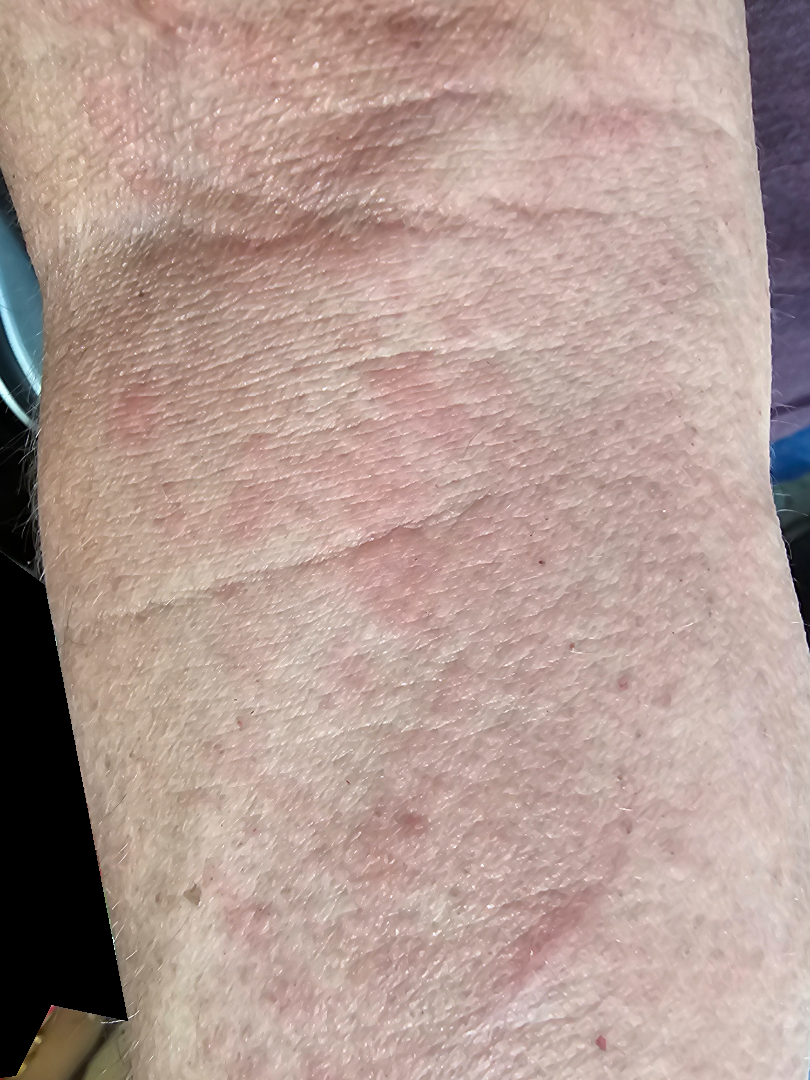Clinical context:
Reported lesion symptoms include itching and enlargement. Located on the front of the torso and arm. The photograph is a close-up of the affected area. Fitzpatrick skin type III; lay reviewers estimated 2 on the MST. The patient described the issue as a rash.
Assessment:
On dermatologist assessment of the image, Photodermatitis (0.33); Eczema (0.33); Allergic Contact Dermatitis (0.33).